This is a close-up image, the lesion involves the front of the torso.
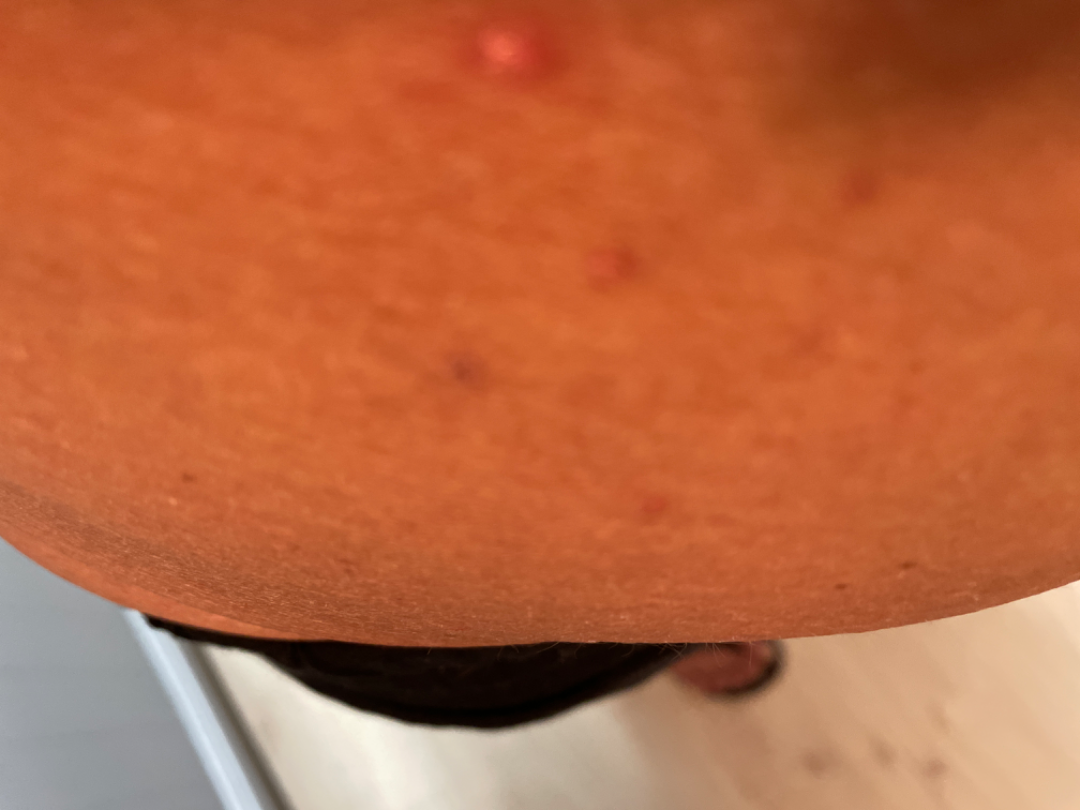The image was not sufficient for the reviewer to characterize the skin condition.